No constitutional symptoms were reported · the patient notes the lesion is raised or bumpy · an image taken at an angle · the leg is involved · present for about one day · the patient notes itching:
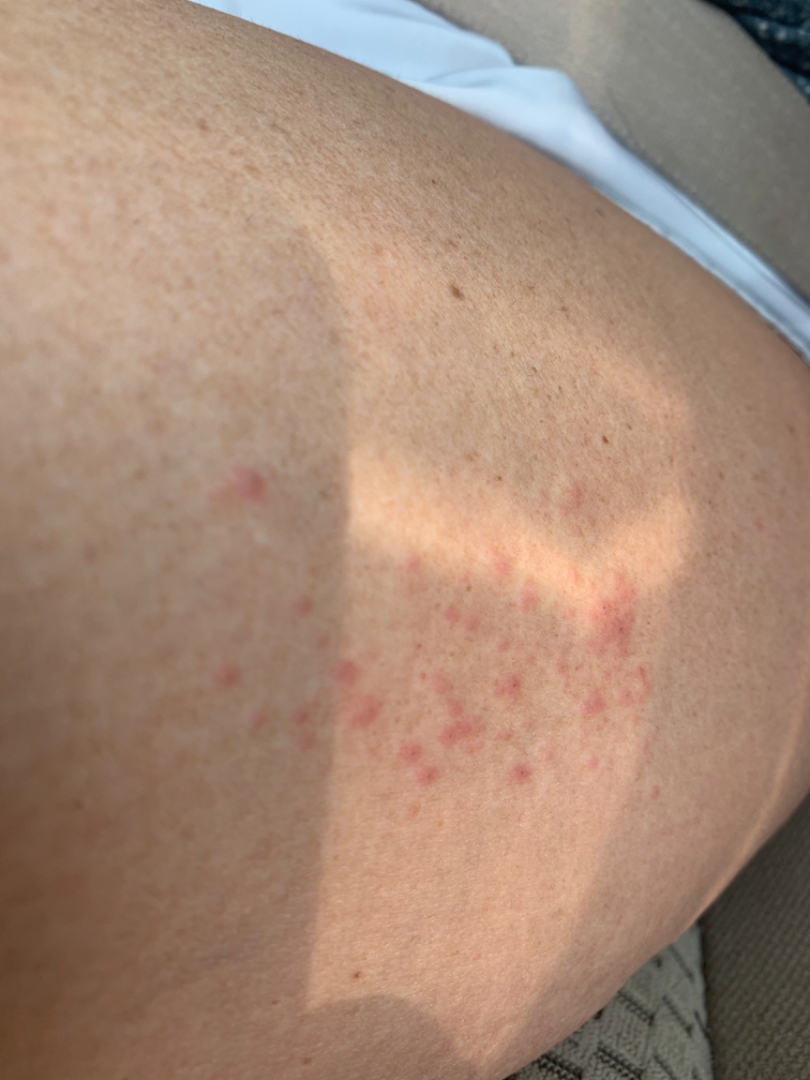Folliculitis (0.50); Irritant Contact Dermatitis (0.50).